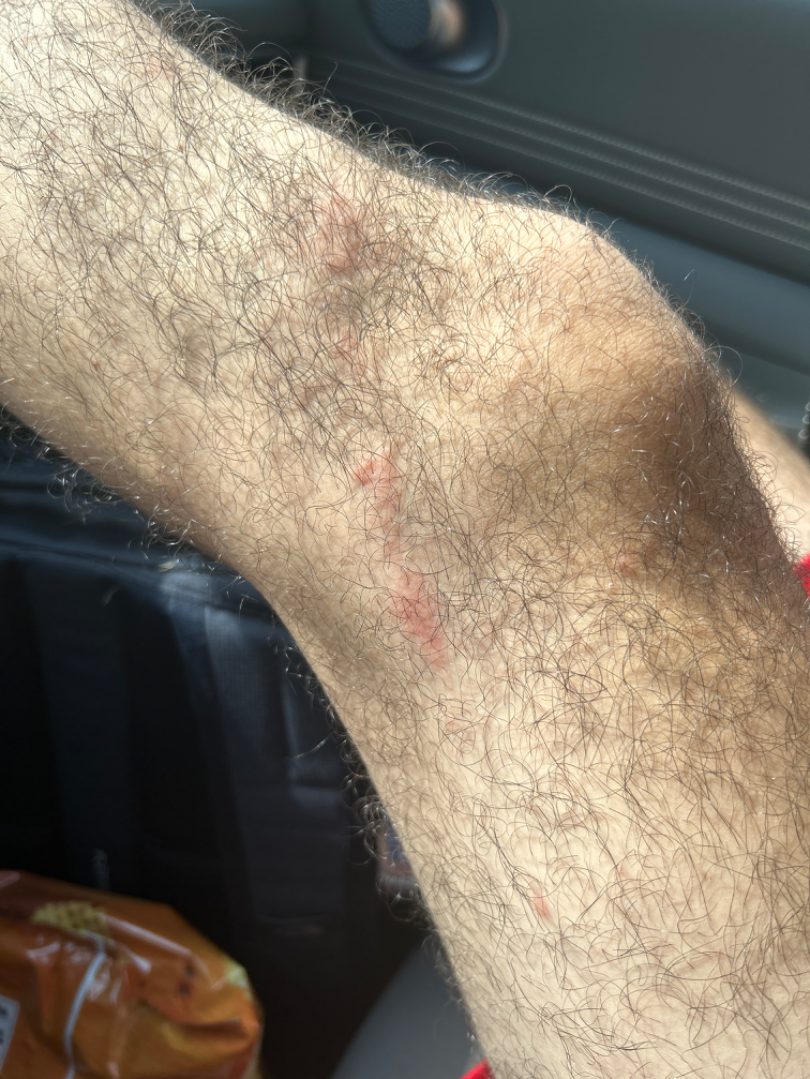Findings:
* assessment · not assessable
* patient-reported symptoms · itching and bothersome appearance
* constitutional symptoms · fatigue
* subject · male, age 18–29
* framing · at a distance
* present for · less than one week
* site · leg and arm
* self-categorized as · a rash